A dermatoscopic image of a skin lesion: 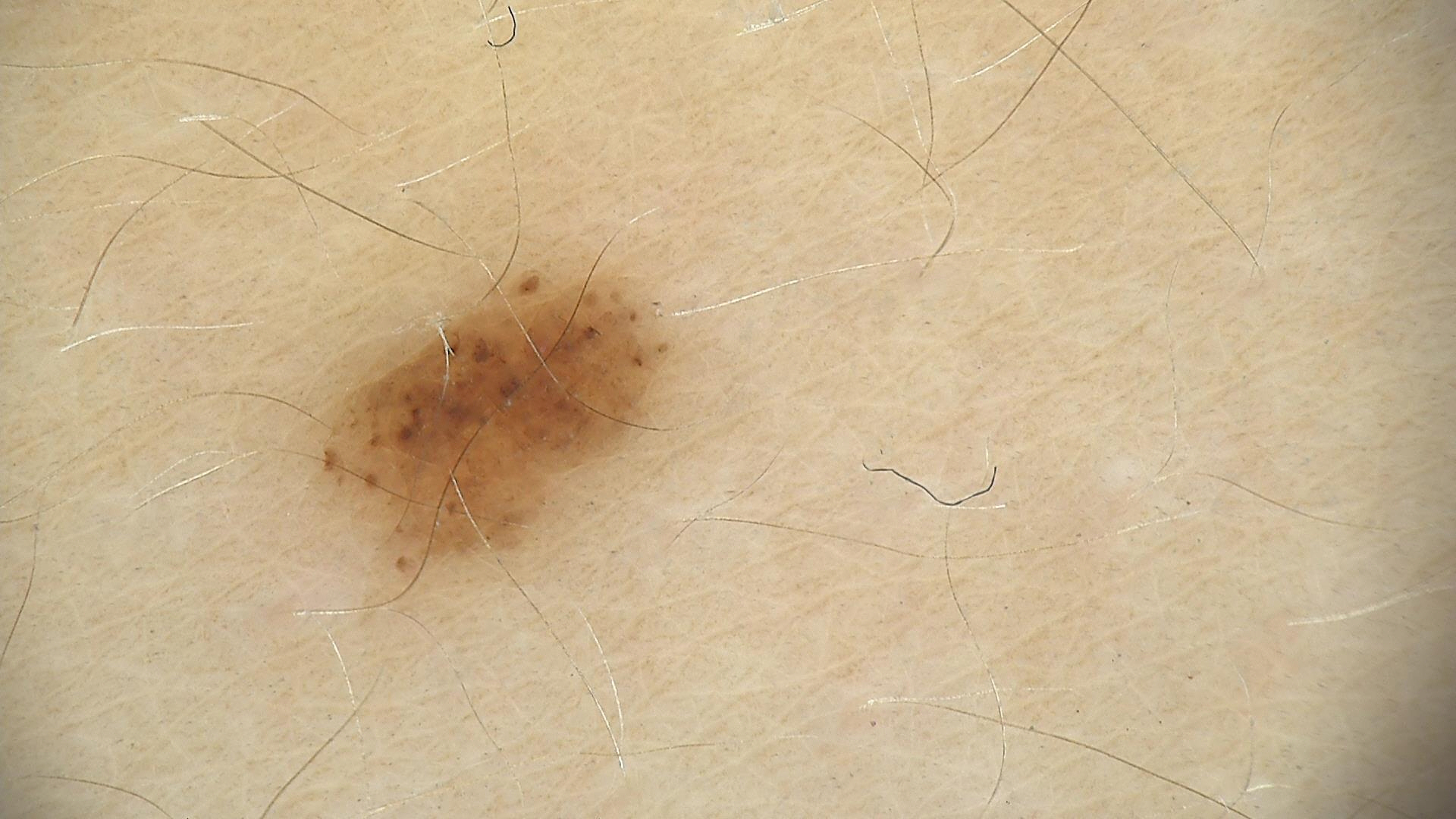The diagnosis was a dysplastic junctional nevus.